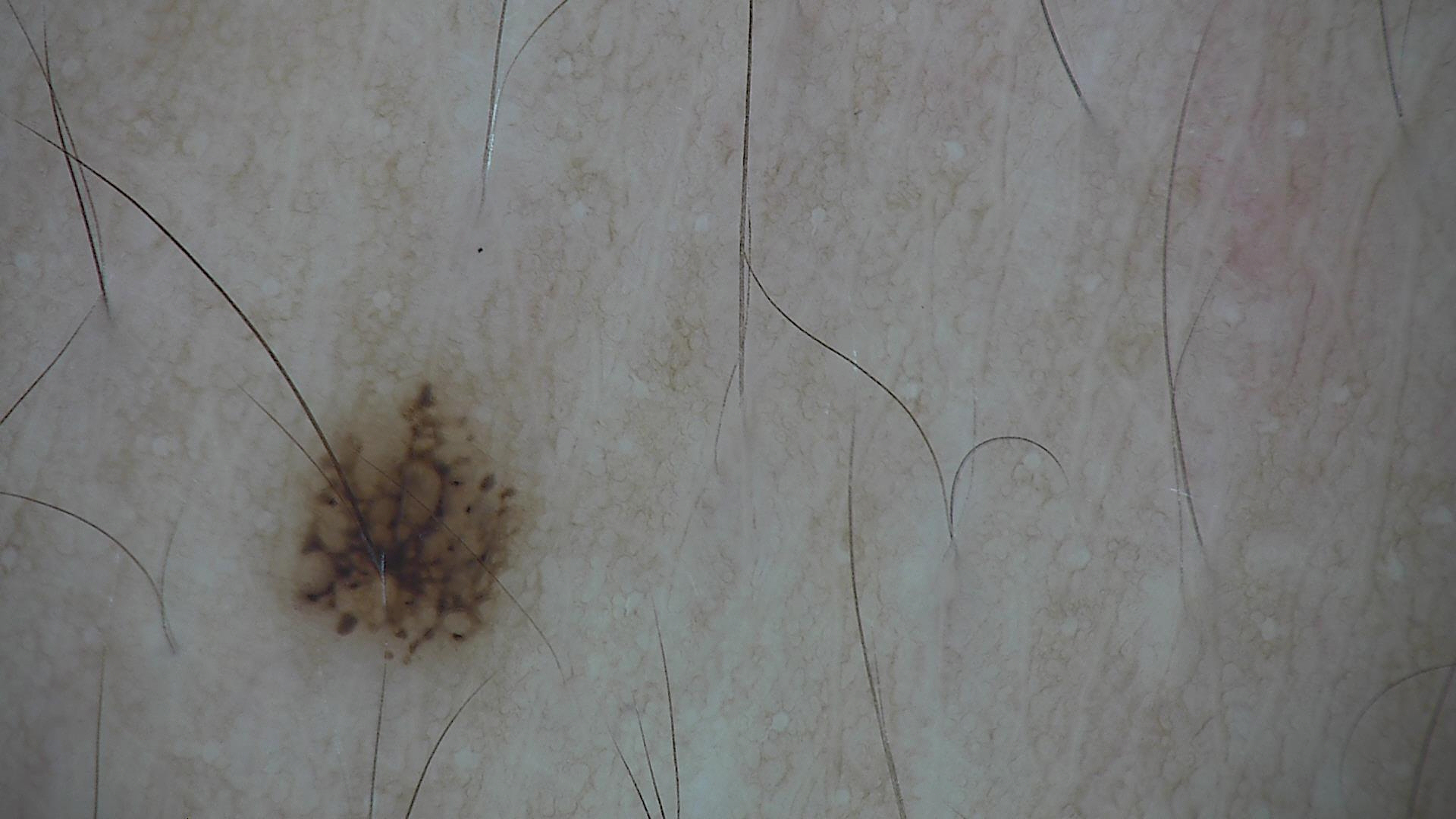Findings:
• image type — dermoscopy
• class — dysplastic junctional nevus (expert consensus)